The lesion involves the front of the torso, leg and arm. The photograph is a close-up of the affected area:
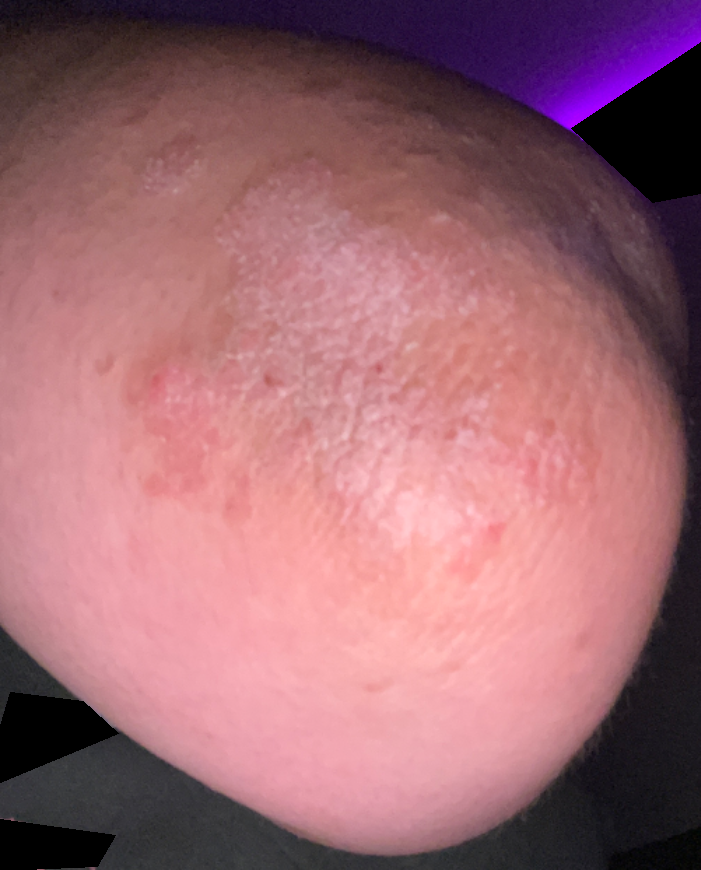Psoriasis (100%).